The subject is 30–39, female; the photograph is a close-up of the affected area: 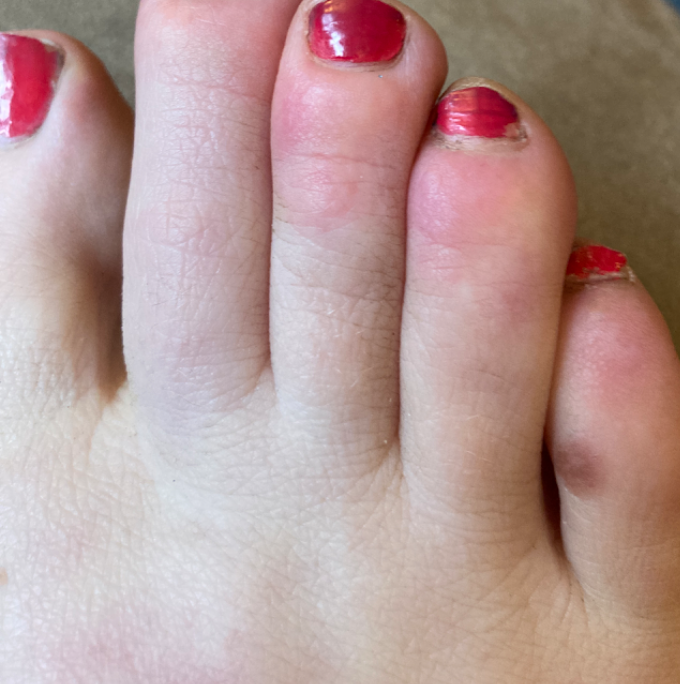Background: The lesion is described as raised or bumpy. Present for one to four weeks. Findings: Chilblain (leading); Eczema (possible); Allergic Contact Dermatitis (possible).